Dermoscopy of a skin lesion: 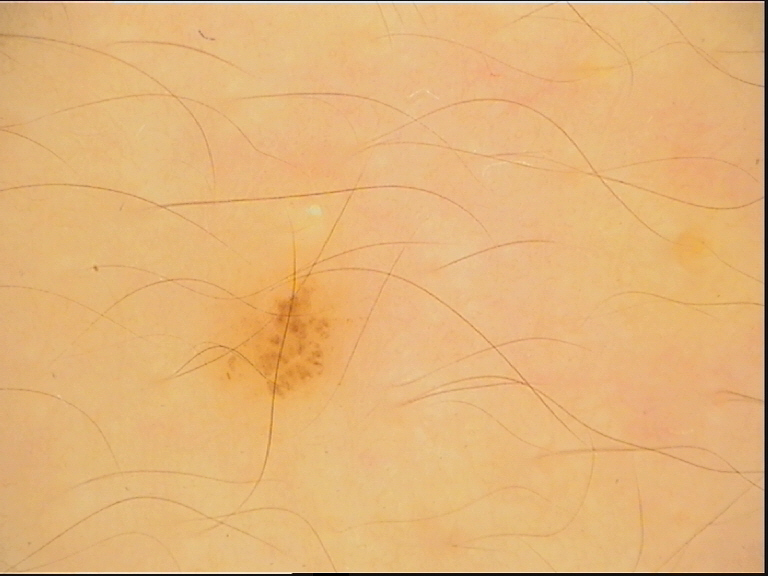The diagnosis was a benign lesion — a dysplastic junctional nevus.